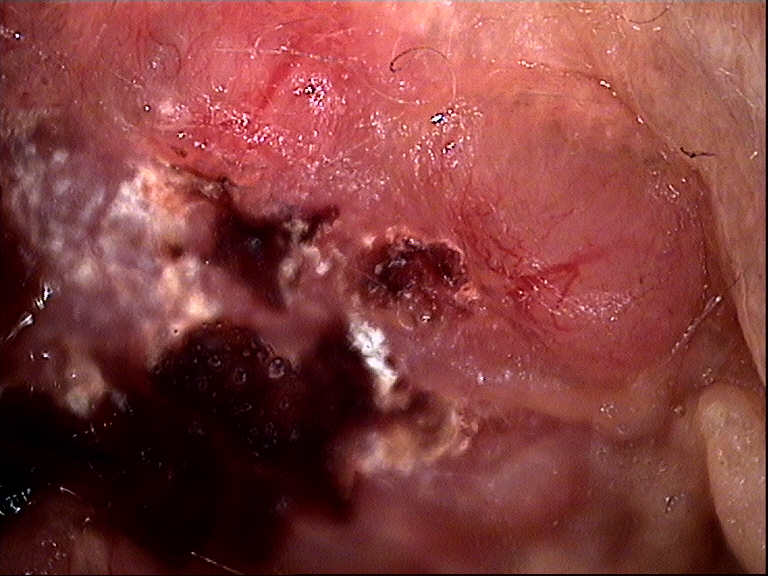A dermoscopic close-up of a skin lesion. The architecture is that of a keratinocytic lesion. Histopathologically confirmed as a malignant lesion — a basal cell carcinoma.